Female contributor, age 40–49. Close-up view. The lesion involves the arm — 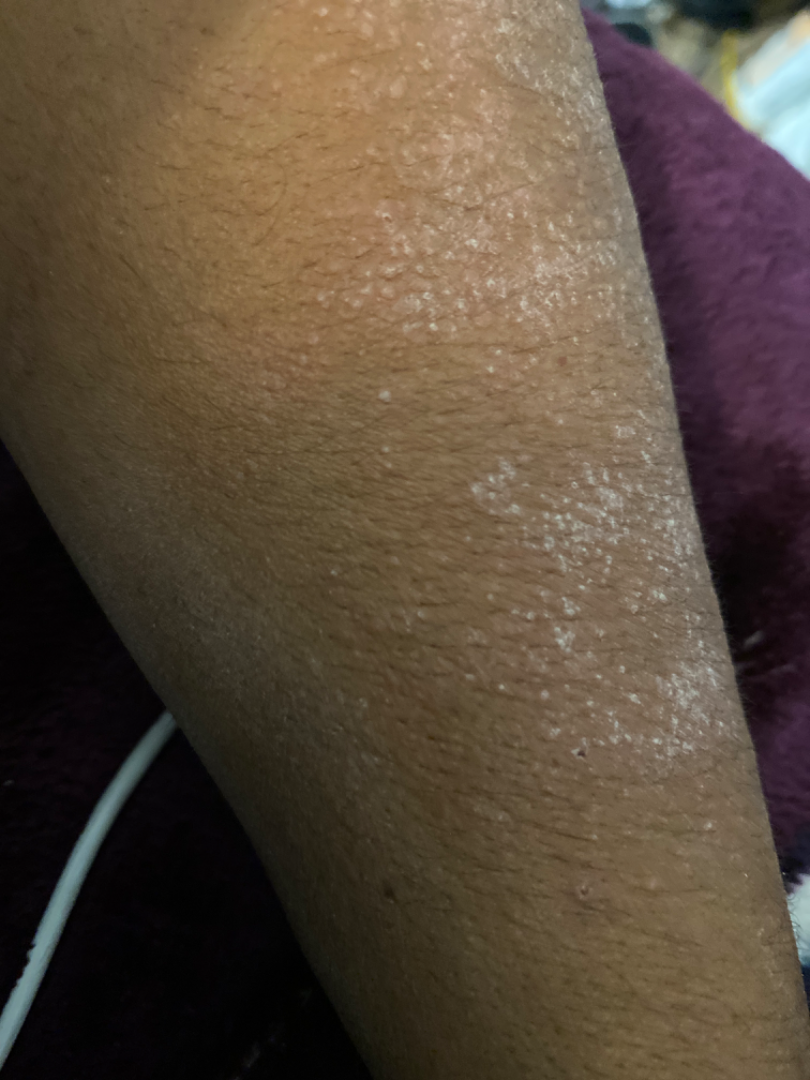Notes:
• assessment: not assessable
• patient's own categorization: a rash
• onset: one to four weeks
• reported symptoms: bothersome appearance and itching
• described texture: raised or bumpy